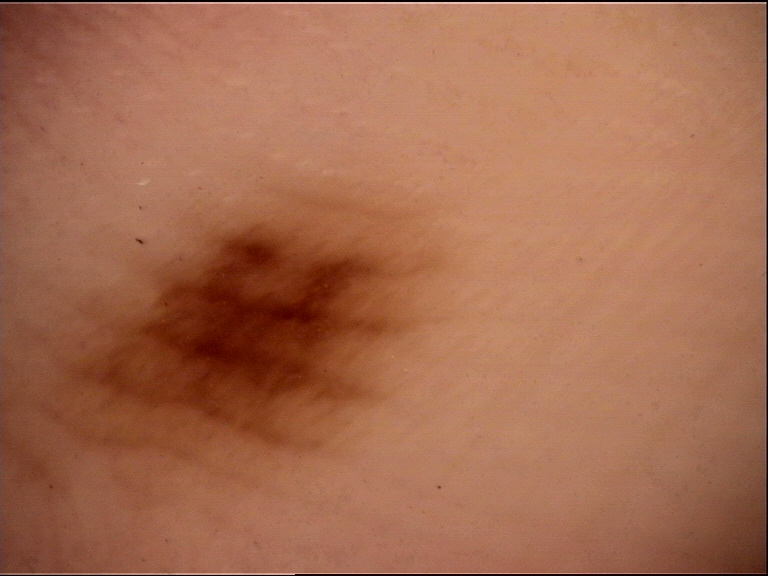Q: What is the diagnosis?
A: acral junctional nevus (expert consensus)